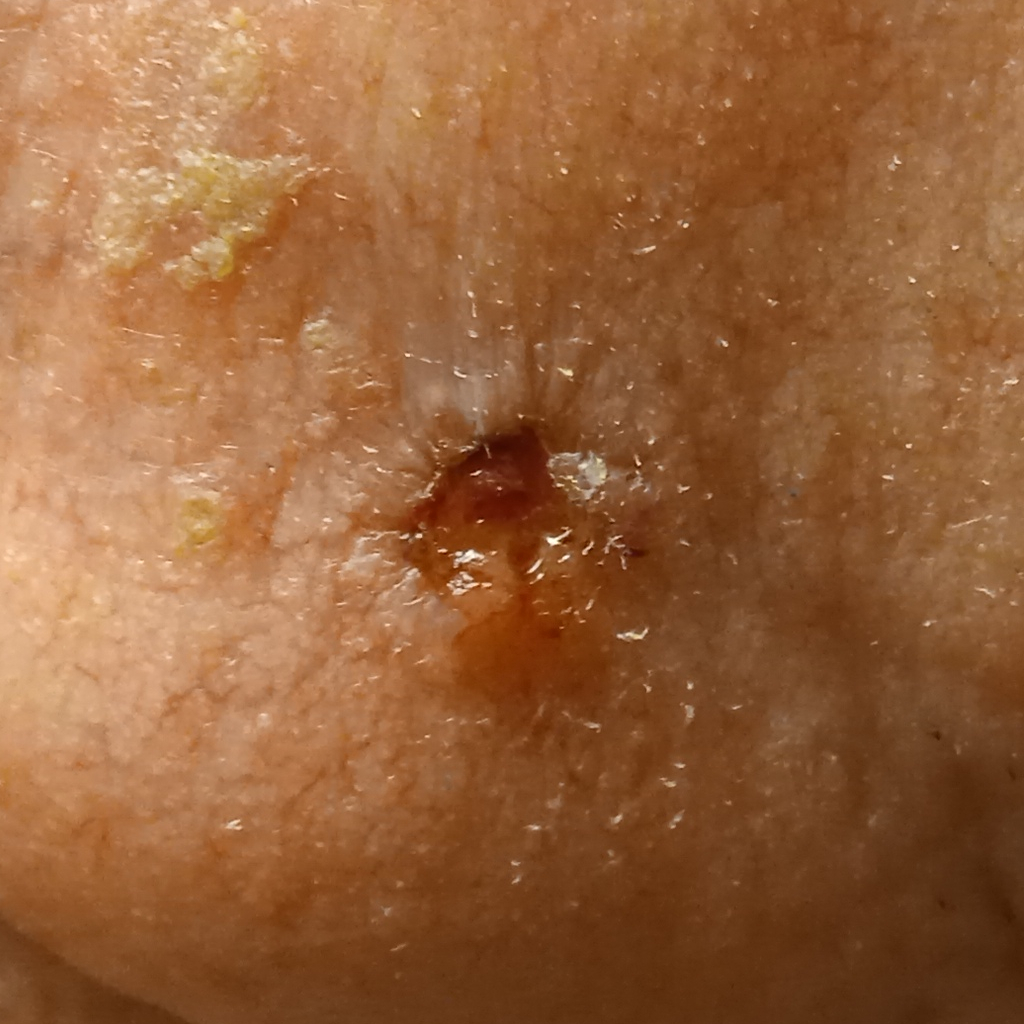Q: What is the imaging modality?
A: clinical photograph
Q: What is the referral context?
A: clinical suspicion of basal cell carcinoma
Q: What is the anatomic site?
A: the face
Q: How large is the lesion?
A: 8.5 mm
Q: What did the biopsy show?
A: basal cell carcinoma (biopsy-proven)